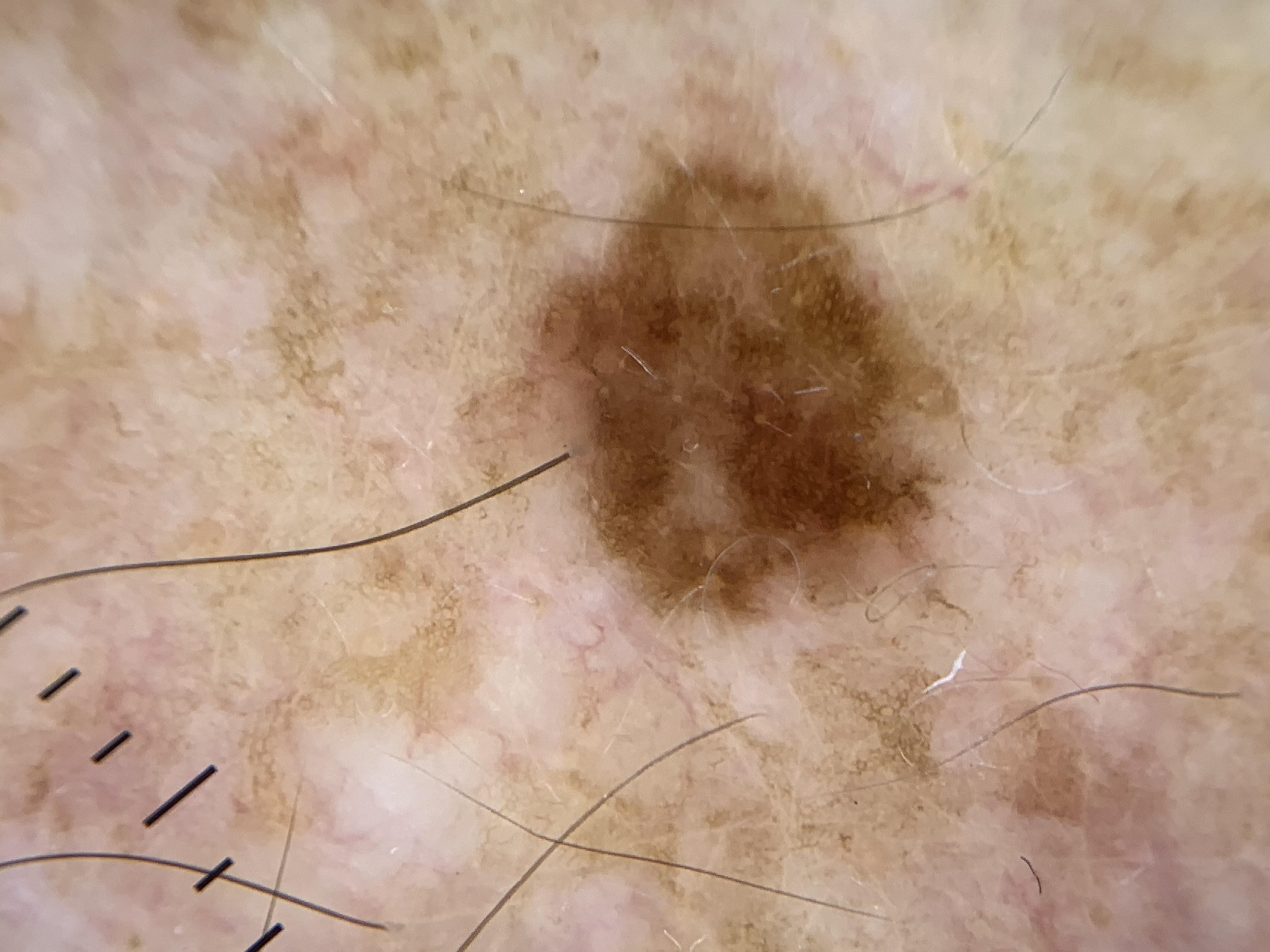{"skin_type": "II", "melanoma_history": {"personal_hx_melanoma": true}, "patient": {"age_approx": 60, "sex": "male"}, "image": "contact-polarized dermoscopy", "diagnosis": {"name": "Nevus", "malignancy": "benign", "confirmation": "histopathology", "lineage": "melanocytic"}}